A female subject age 60; the patient reports a personal history of skin cancer and a personal history of cancer; the patient says their skin tans without first burning; the referring clinician suspected basal cell carcinoma; the patient describes having few moles overall; dermoscopy of a skin lesion.
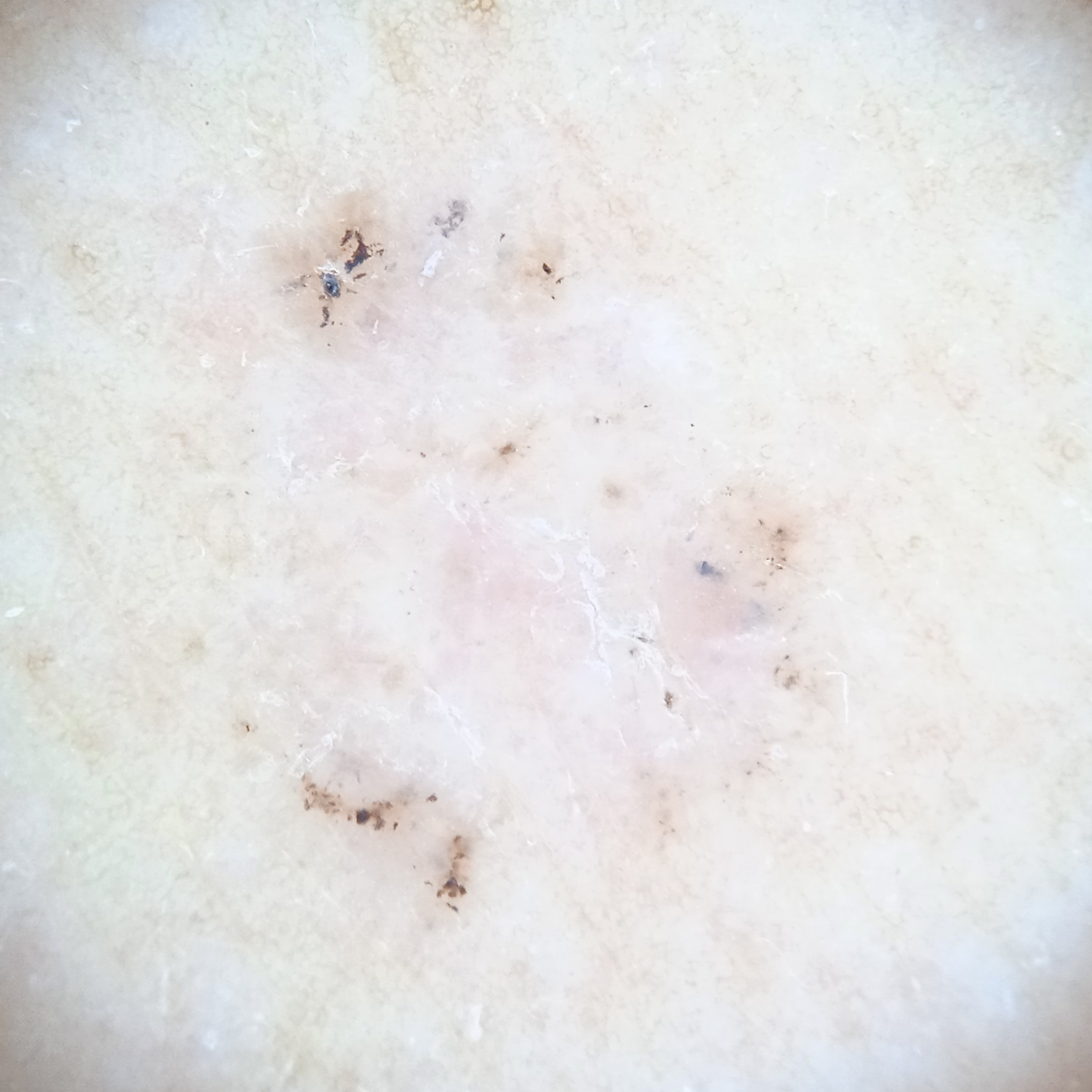Summary:
The lesion is on the back.
Conclusion:
The dermatologists' assessment was a basal cell carcinoma.